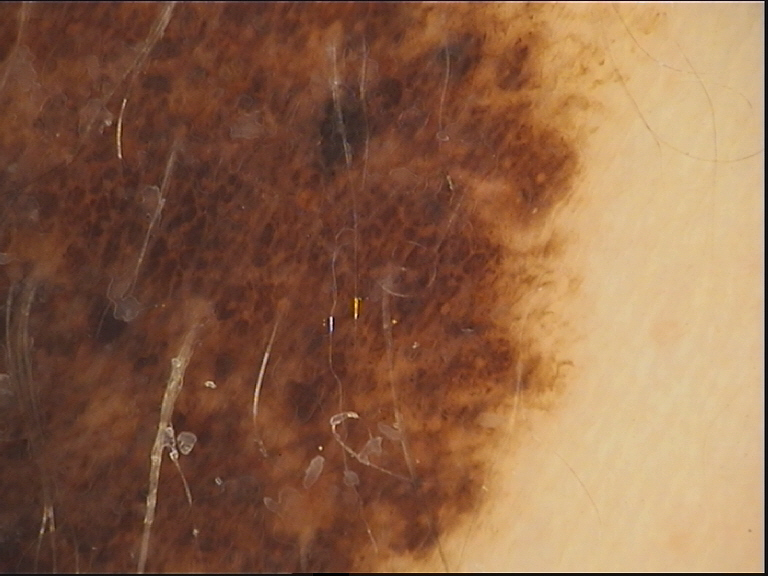Summary: A dermatoscopic image of a skin lesion. The morphology is that of a banal lesion. Impression: Diagnosed as a congenital compound nevus.